A dermoscopic image of a skin lesion.
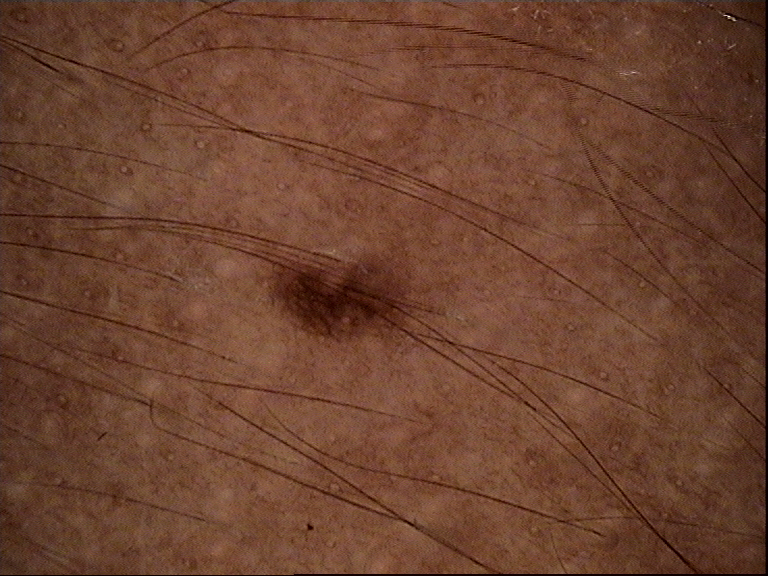classification = banal; label = junctional nevus (expert consensus).